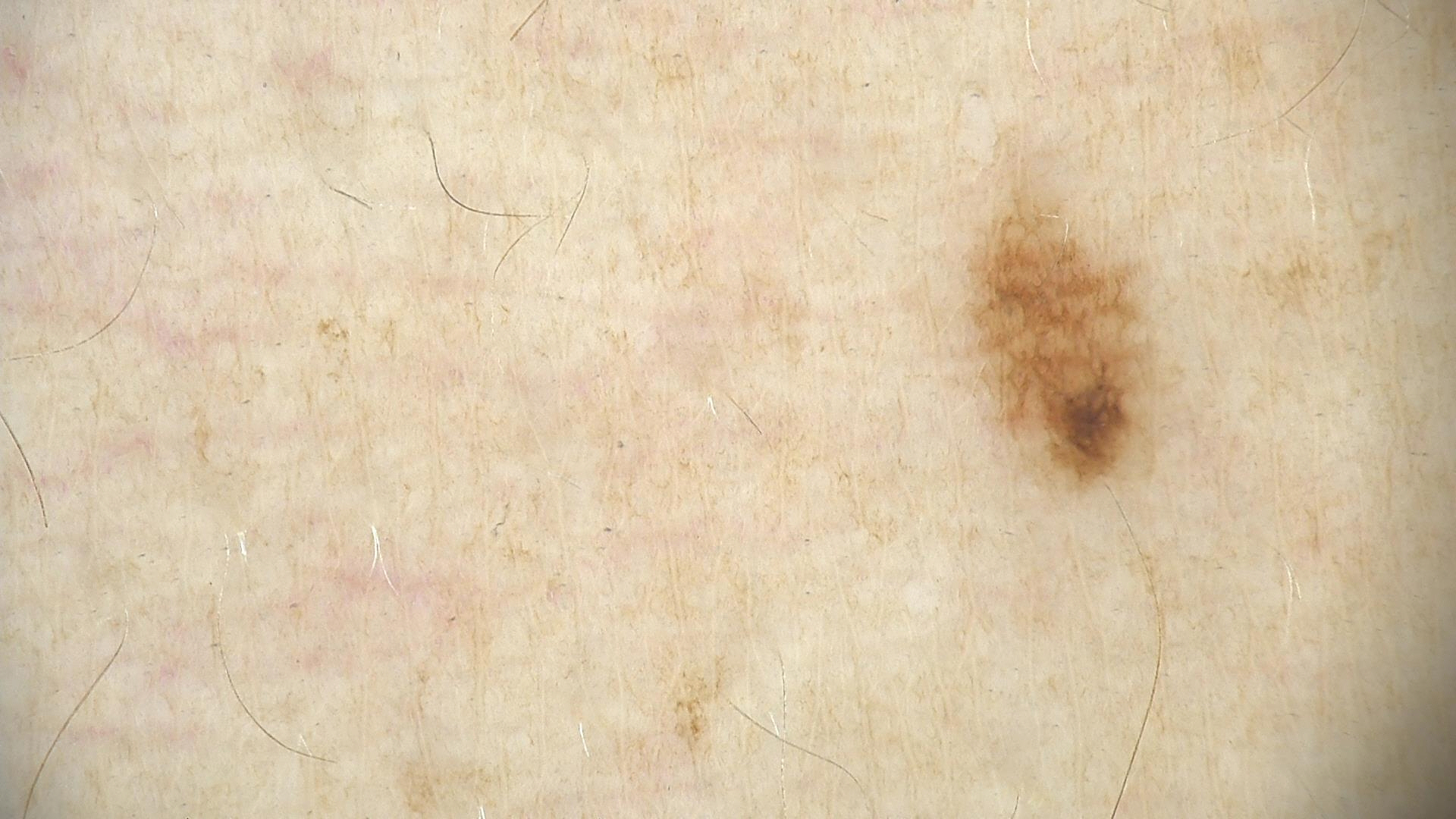A skin lesion imaged with a dermatoscope. Diagnosed as a dysplastic junctional nevus.